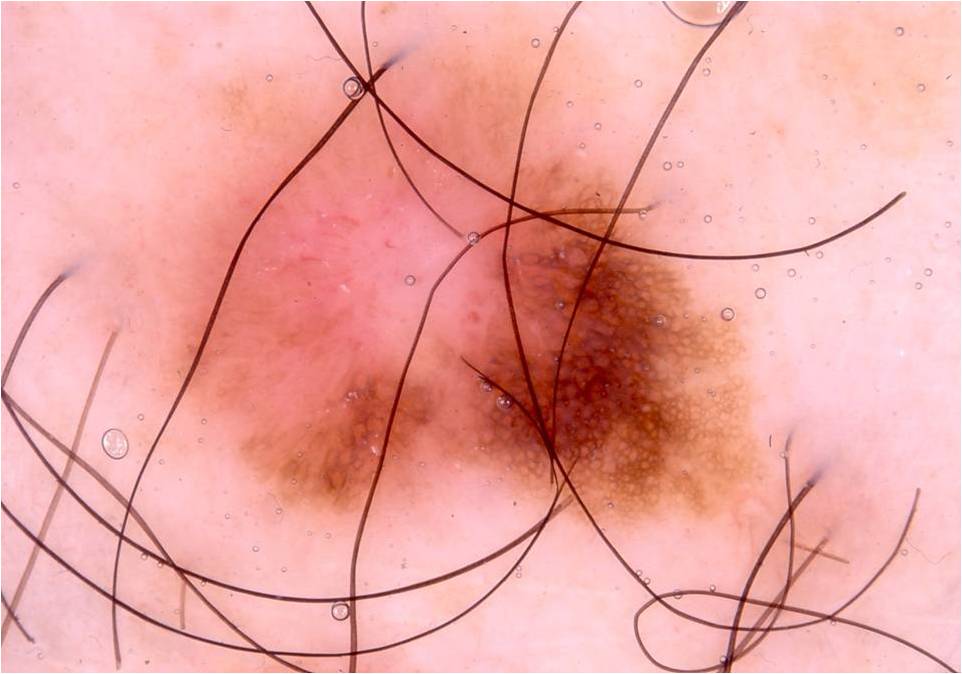Image and clinical context:
The subject is a male aged 33 to 37. A dermoscopic image of a skin lesion. On dermoscopy, the lesion shows pigment network. Lesion location: 145 7 770 545. The lesion occupies roughly 37% of the field.
Assessment:
The clinical diagnosis was a melanocytic nevus.